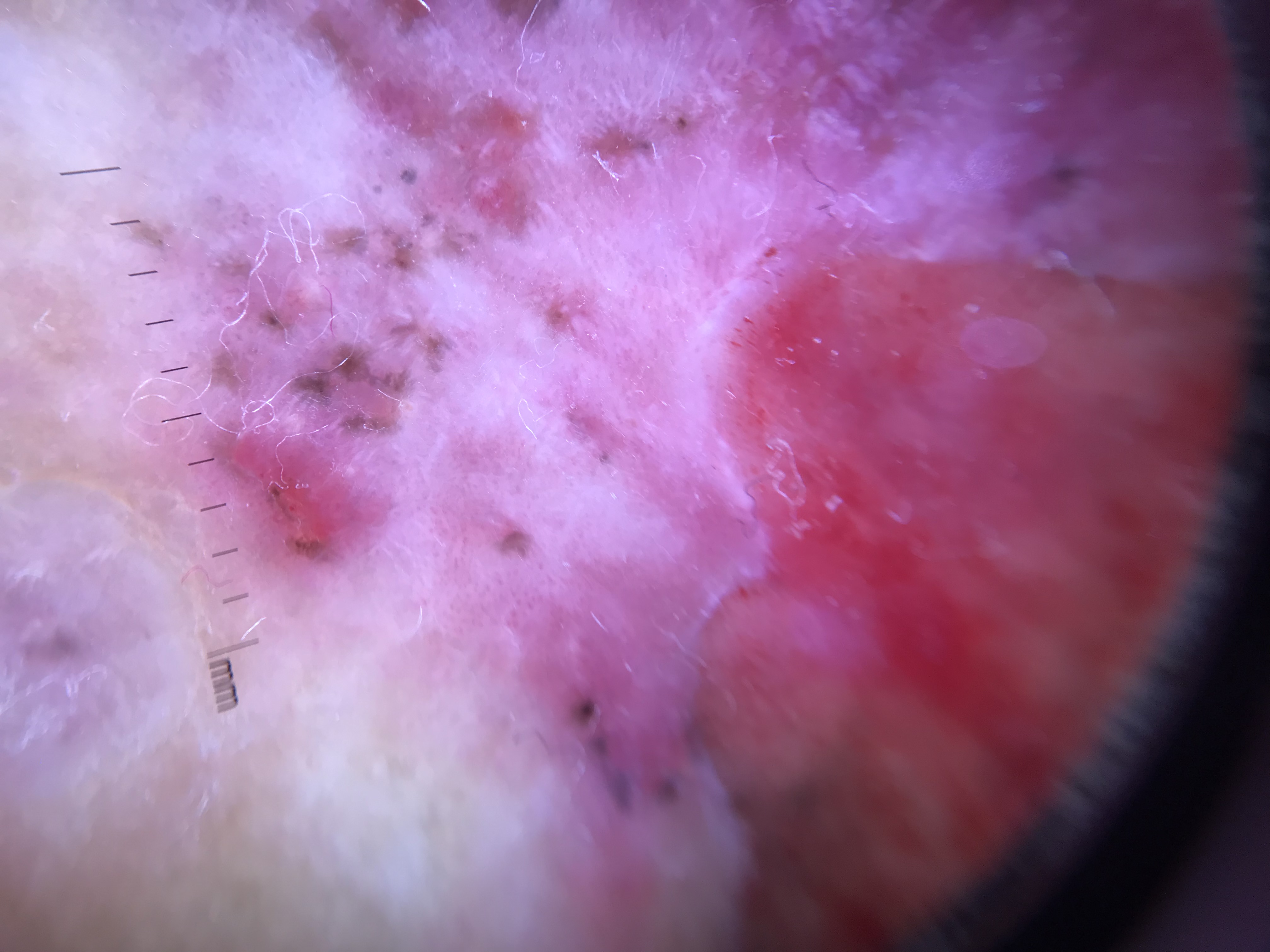A dermoscopic image of a skin lesion. Histopathologically confirmed as a malignancy — a basal cell carcinoma.